The patient is 40–49, female; the photo was captured at a distance; located on the top or side of the foot:
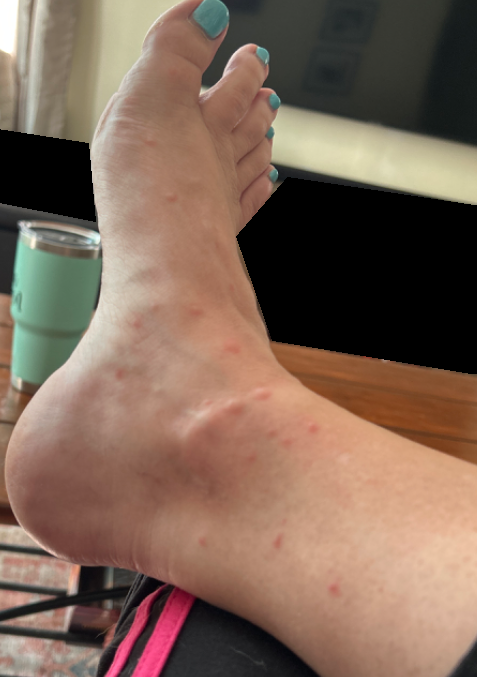Review: The dermatologist could not determine a likely condition from the photograph alone.